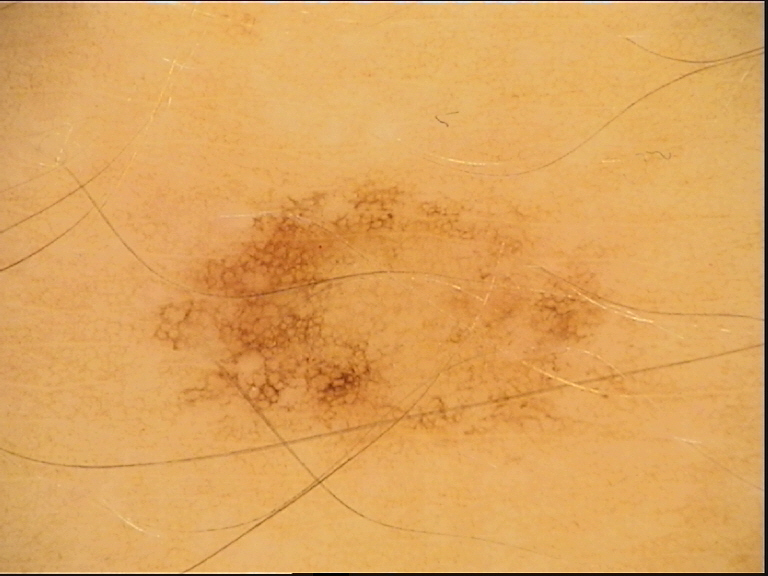A dermatoscopic image of a skin lesion. The diagnostic label was a dysplastic junctional nevus.